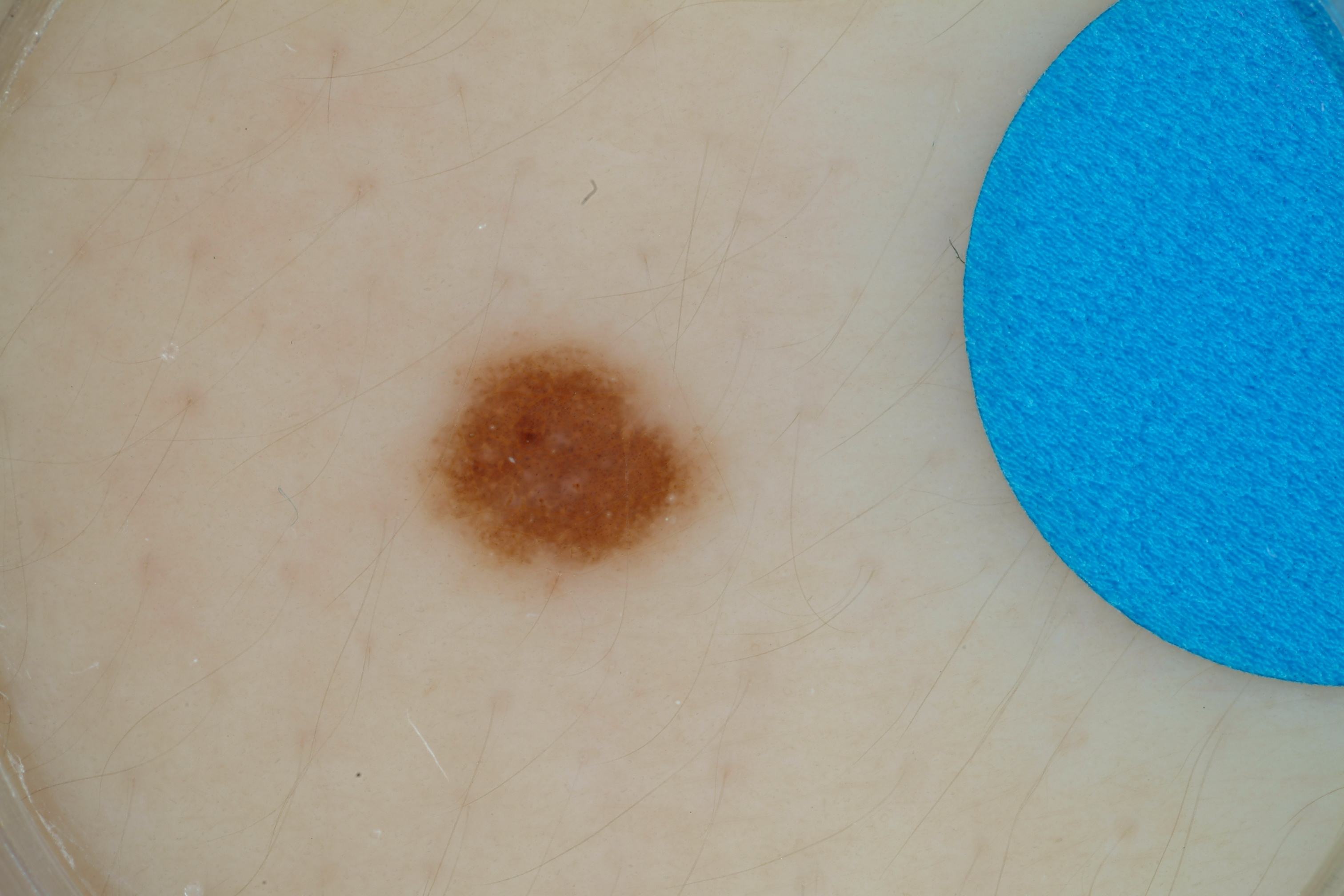modality — dermoscopic image | subject — male, about 15 years old | features — globules, pigment network, and milia-like cysts; absent: streaks and negative network | size — small | location — left=373, top=318, right=727, bottom=605 | impression — a melanocytic nevus, a benign lesion.